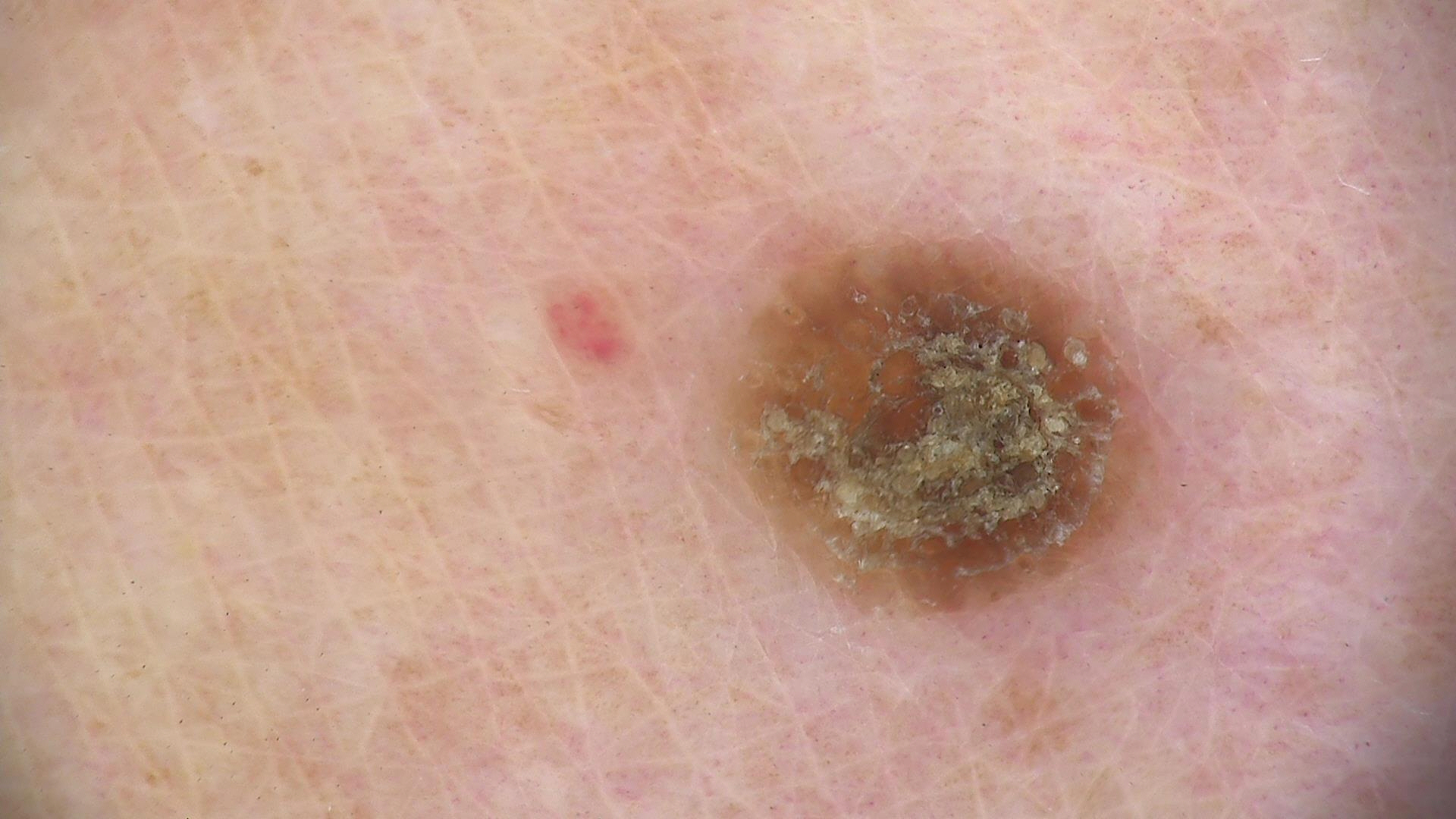| field | value |
|---|---|
| diagnostic label | seborrheic keratosis (expert consensus) |